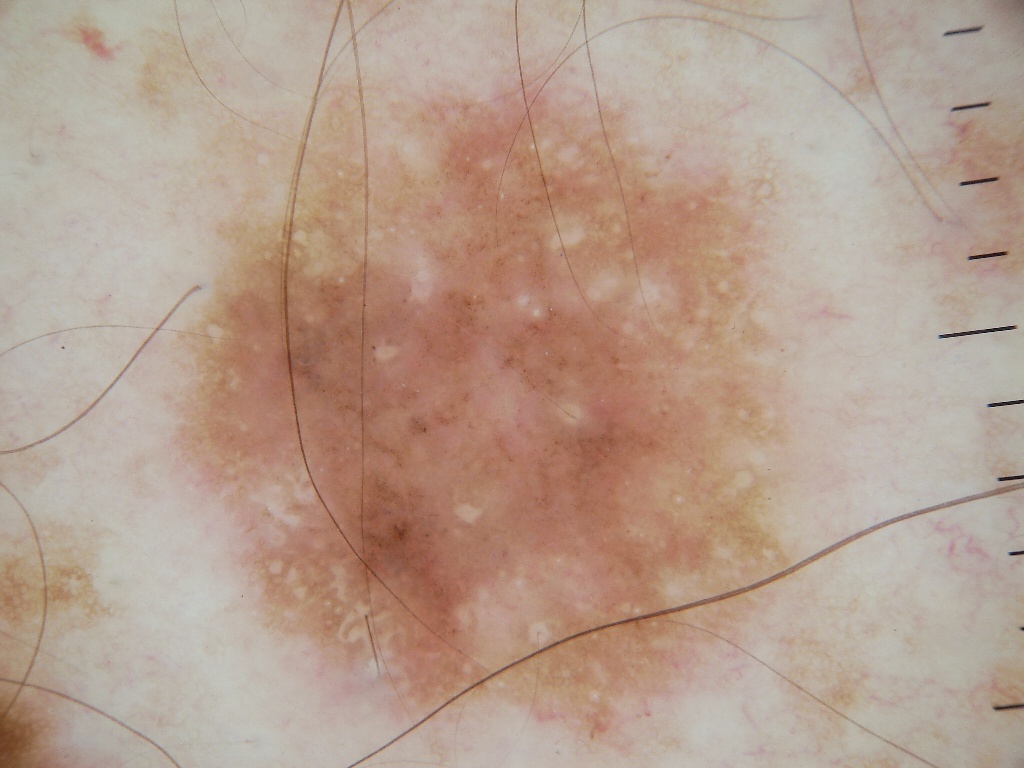Dermoscopy of a skin lesion.
The lesion is bounded by x1=163, y1=39, x2=813, y2=758.
The lesion takes up about 50% of the image.
Clinically diagnosed as a benign skin lesion.